The photograph was taken at a distance:
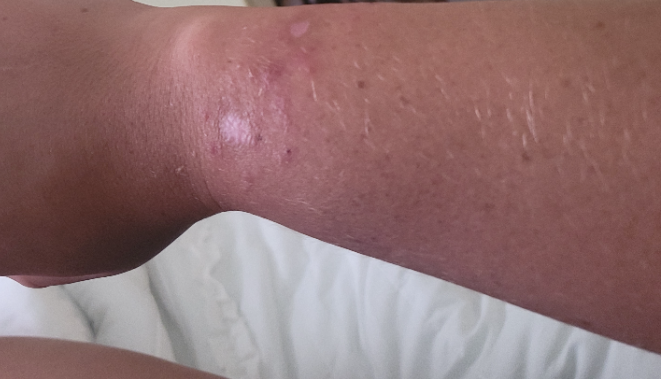Findings:
On dermatologist assessment of the image: most consistent with Allergic Contact Dermatitis; an alternative is Acute and chronic dermatitis.